The contributor is 18–29, male. The photo was captured at a distance. Self-categorized by the patient as a rash. The affected area is the leg.
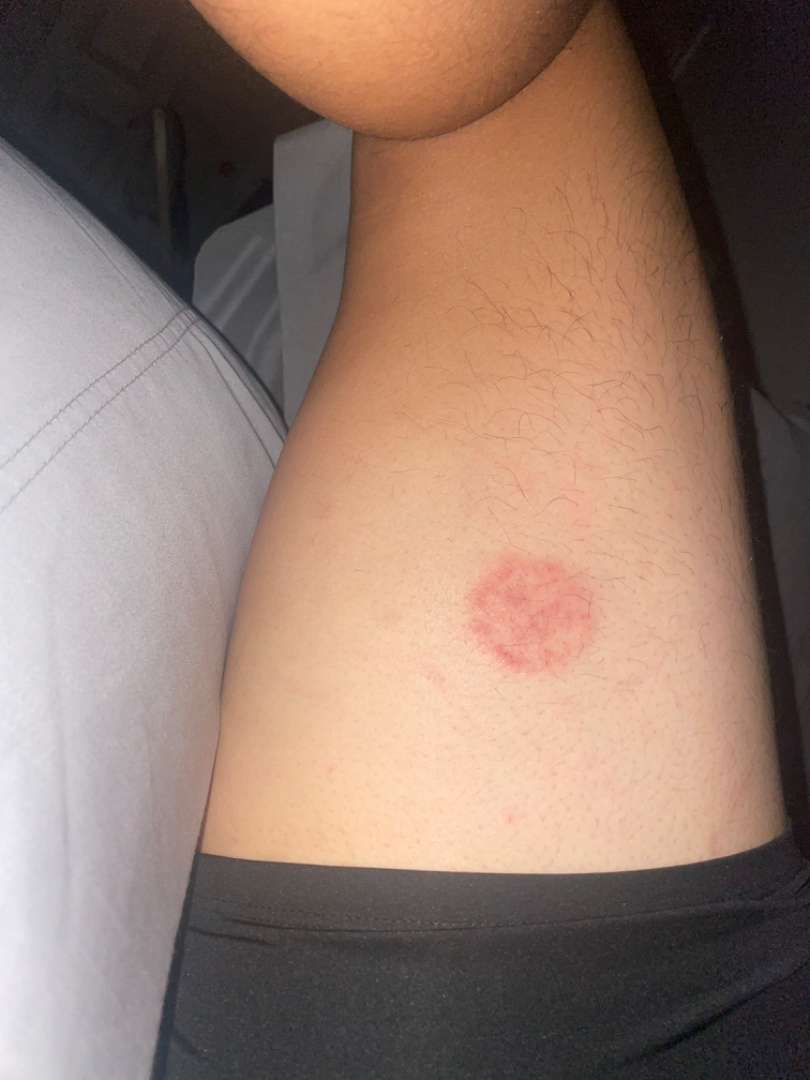Three dermatologists each reviewed the case: the leading consideration is Eczema; also consider Tinea; lower on the differential is Allergic Contact Dermatitis.